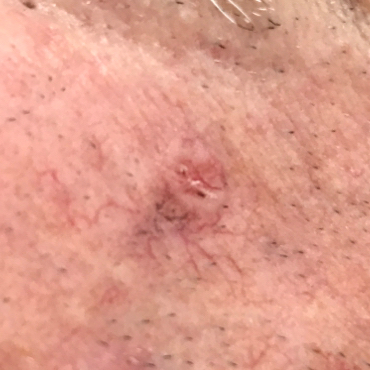Clinical context:
A male patient 84 years old. History notes alcohol use, prior skin cancer (patient or family), tobacco use, no prior malignancy (patient or family), and no pesticide exposure. The patient was assessed as Fitzpatrick phototype II. The patient describes that the lesion is elevated, but does not itch.
Diagnosis:
Histopathologically confirmed as a basal cell carcinoma.